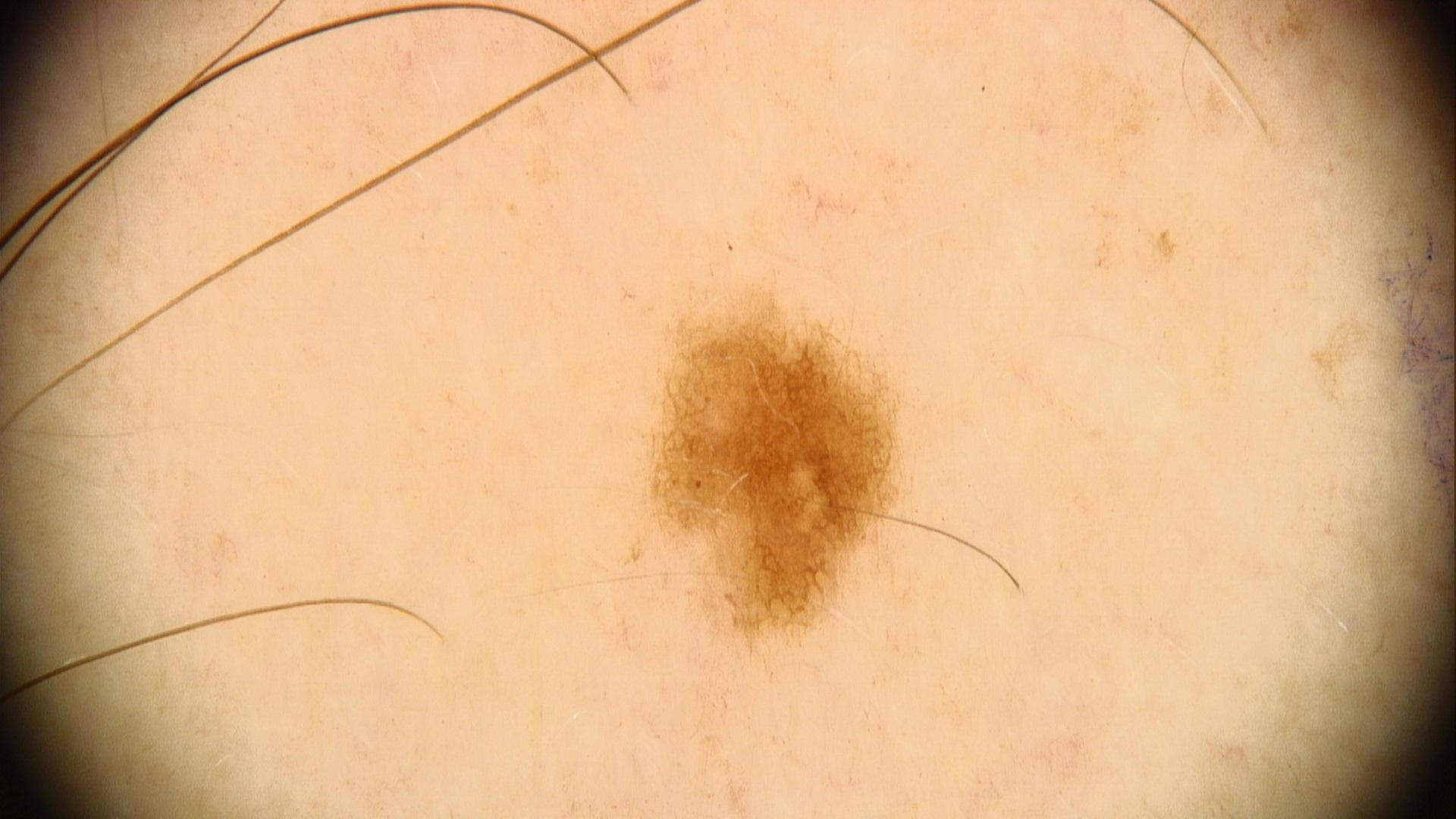The chart documents melanoma in a first-degree relative.
Fitzpatrick phototype III.
A male subject aged approximately 40.
Contact-polarized dermoscopy of a skin lesion.
Expert review favored a lesion of melanocytic lineage — a nevus.